A dermoscopic close-up of a skin lesion:
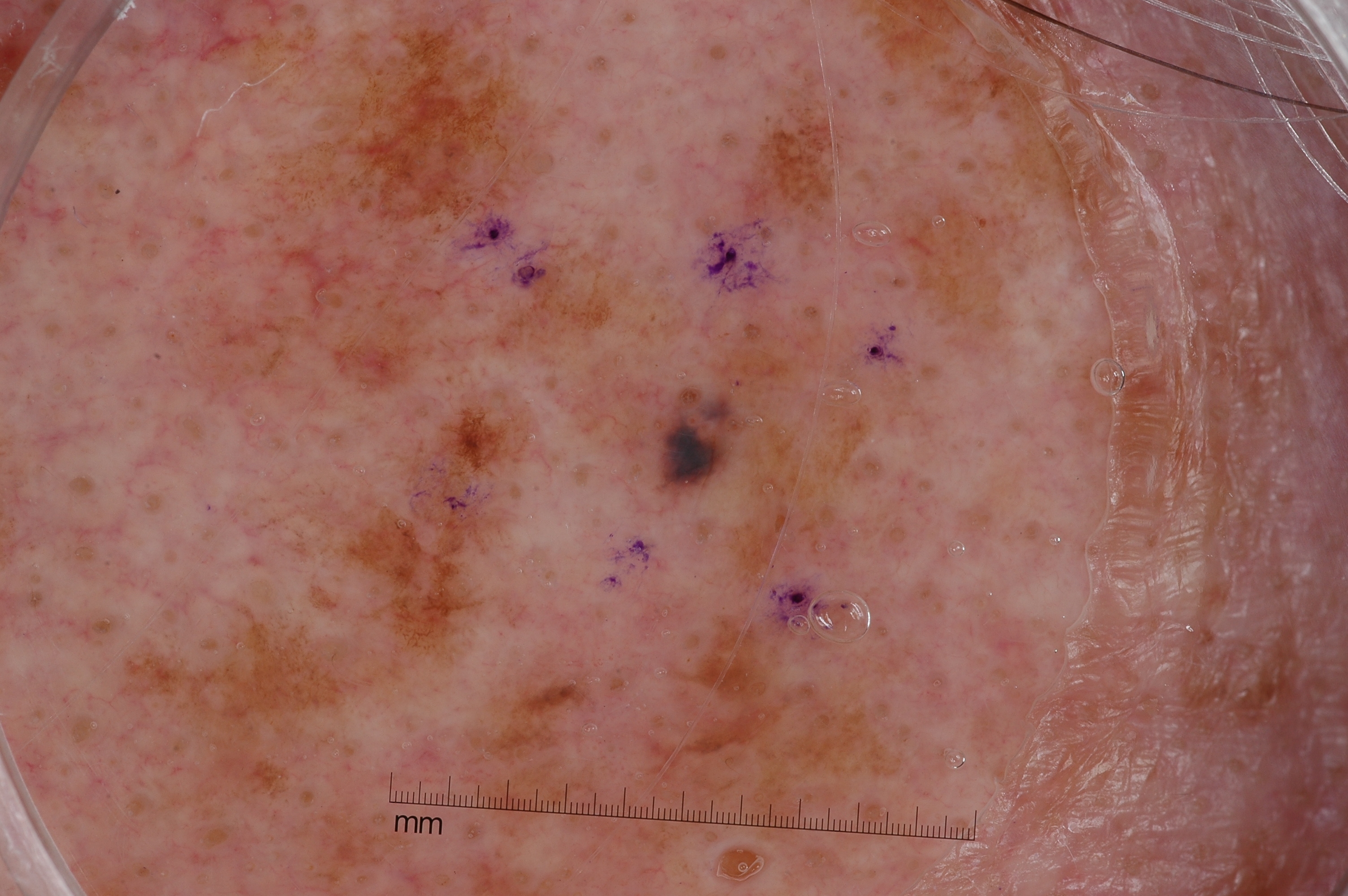| field | value |
|---|---|
| extent | ~7% of the field |
| location | 532, 273, 899, 591 |
| dermoscopic features assessed but absent | pigment network, milia-like cysts, negative network, and streaks |
| assessment | a melanocytic nevus, a benign lesion |